A clinical photo of a skin lesion taken with a smartphone. The chart records prior malignancy (patient or family): 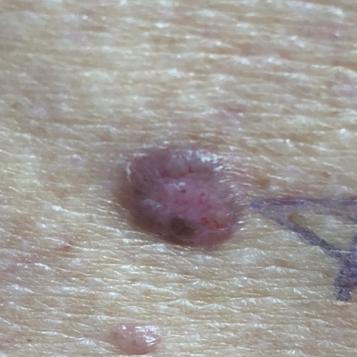• region · the back
• lesion size · 10x7 mm
• symptoms · elevation, growth, itching / no bleeding
• diagnosis · basal cell carcinoma (biopsy-proven)